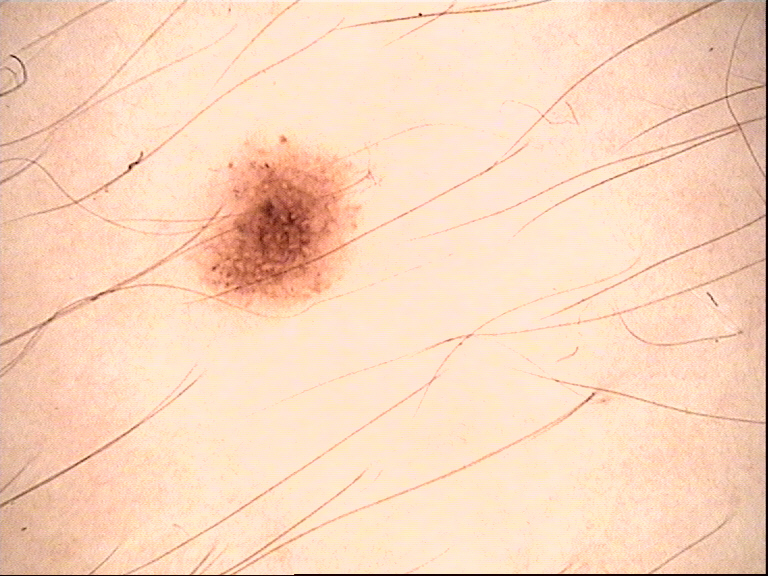Labeled as a dysplastic junctional nevus.